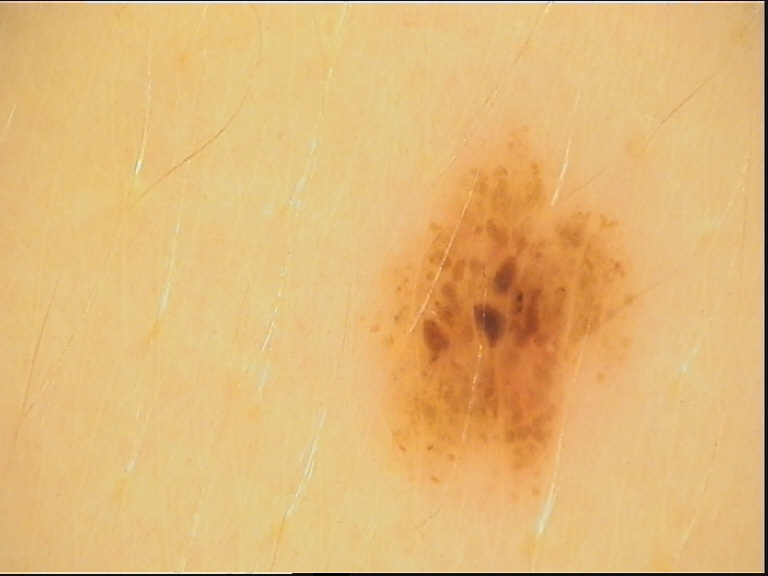A dermoscopic close-up of a skin lesion.
This is a banal lesion.
The diagnostic label was a compound nevus.